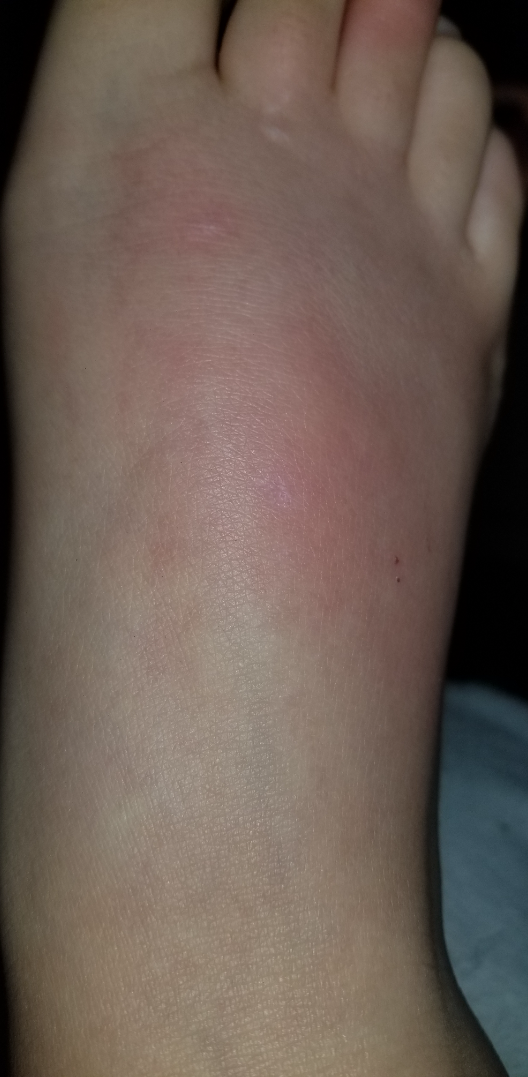Q: Anatomic location?
A: back of the torso, arm and top or side of the foot
Q: Constitutional symptoms?
A: shortness of breath
Q: When did this start?
A: one to four weeks
Q: How does the lesion feel?
A: raised or bumpy
Q: Patient demographics?
A: female, age 18–29
Q: Image view?
A: close-up
Q: What is the differential diagnosis?
A: most likely Urticaria; also raised was Superficial frostbite; with consideration of Insect Bite; less likely is Eczema